An image taken at a distance — 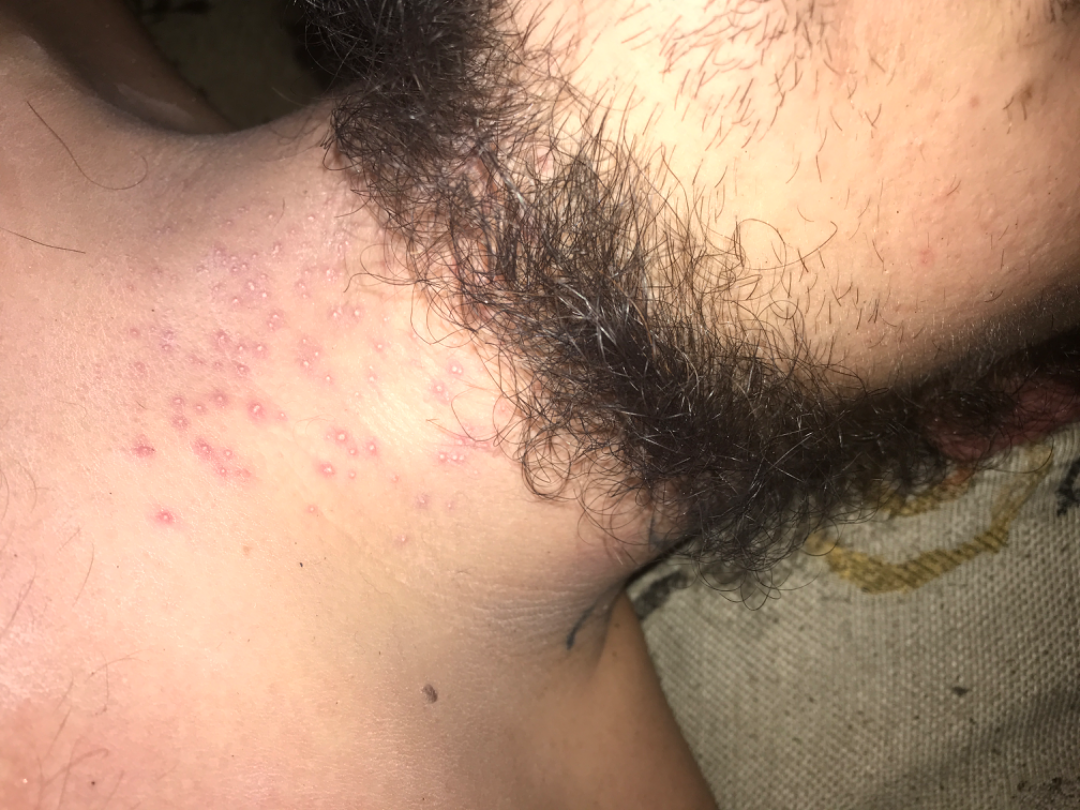skin tone=Fitzpatrick skin type III; lay reviewers estimated Monk skin tone scale 3 or 4 (two reviewer pools) | assessment=the impression on review was Folliculitis.